The photograph is a close-up of the affected area: 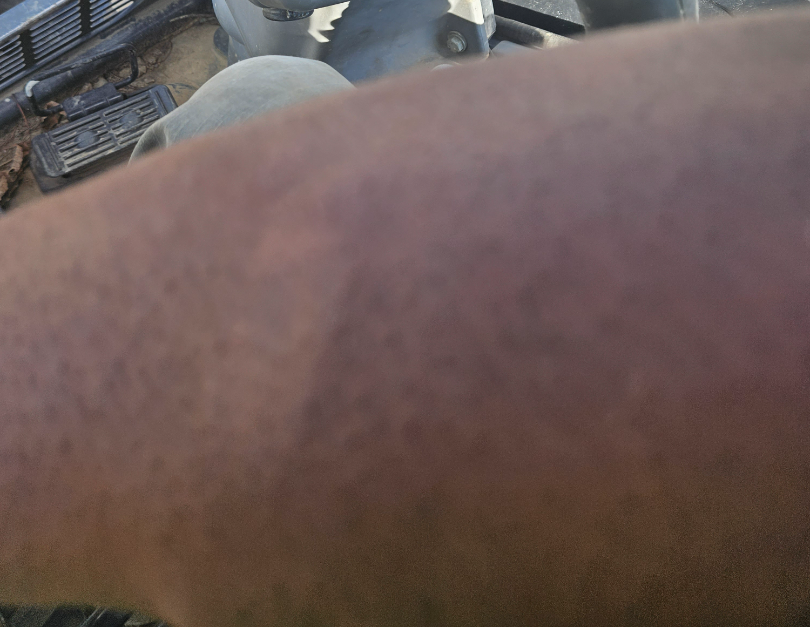The reviewing dermatologist was unable to assign a differential diagnosis from the image.